The photograph was taken at a distance · the lesion is associated with itching · male contributor, age 40–49 · the lesion is described as raised or bumpy · present for less than one week · located on the arm, front of the torso, leg and back of the torso · no relevant systemic symptoms · self-categorized by the patient as a rash — 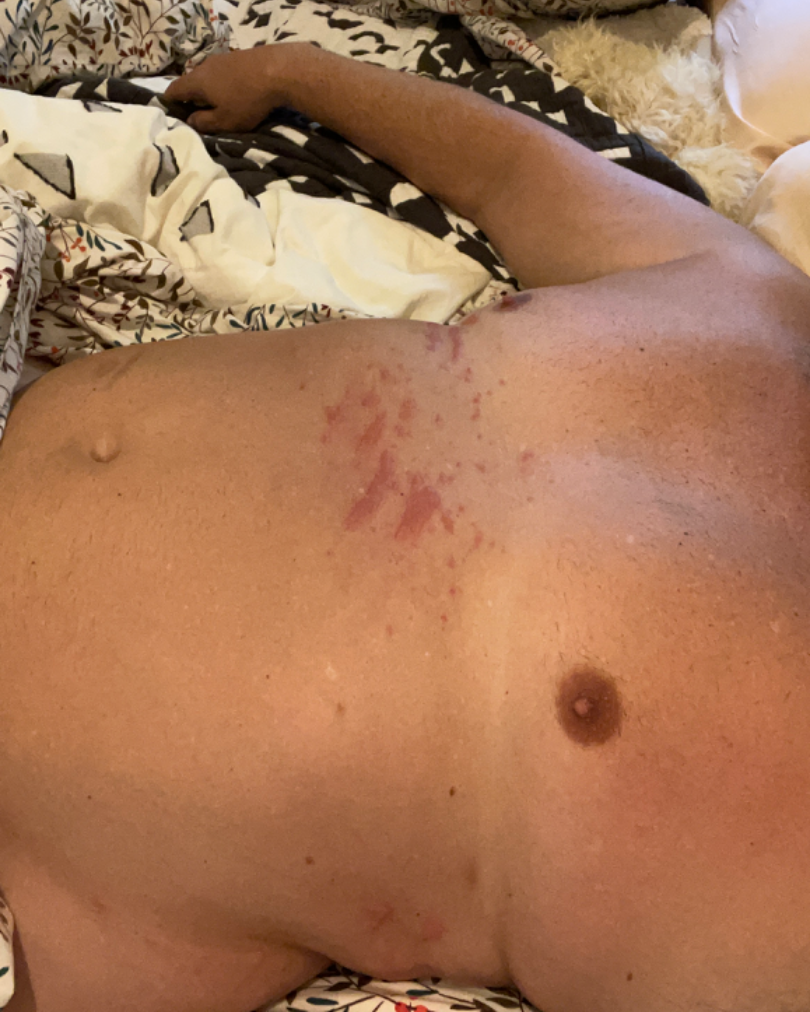Reviewed remotely by one dermatologist: the primary impression is Allergic Contact Dermatitis; an alternative is Herpes Zoster.